This image was taken at a distance:
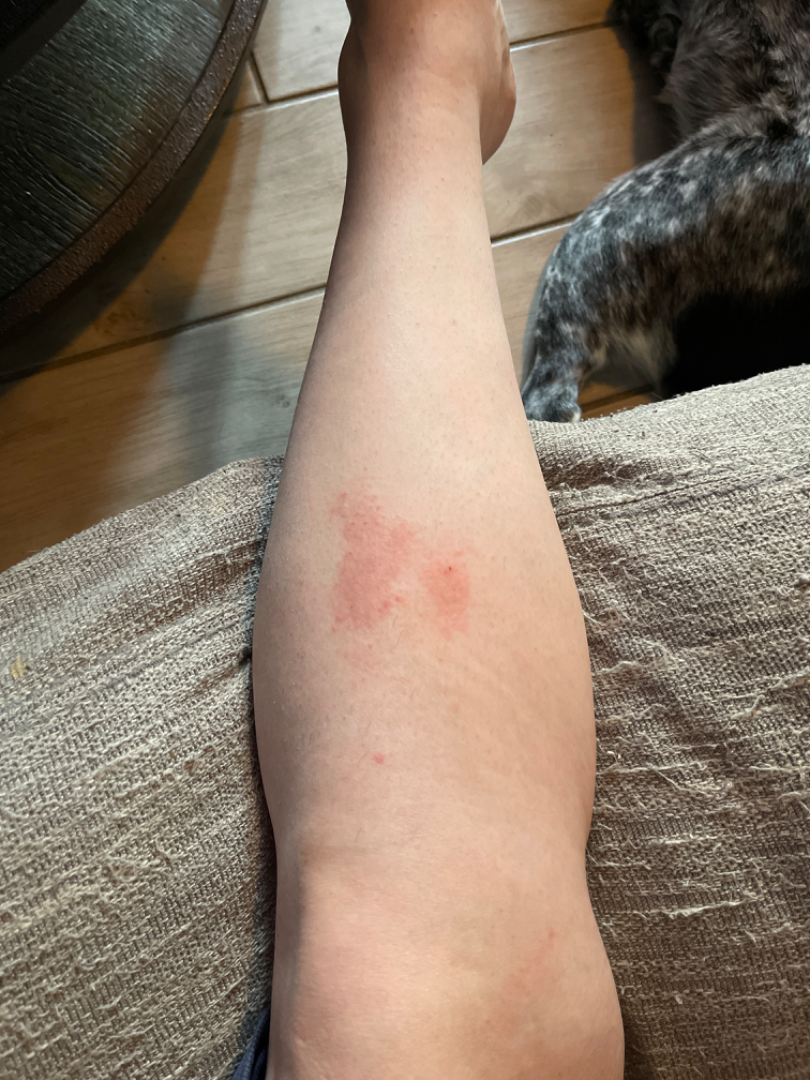assessment: indeterminate from the photograph